A female patient 67 years of age; a dermoscopic image of a skin lesion; the patient says their skin tans without first burning: 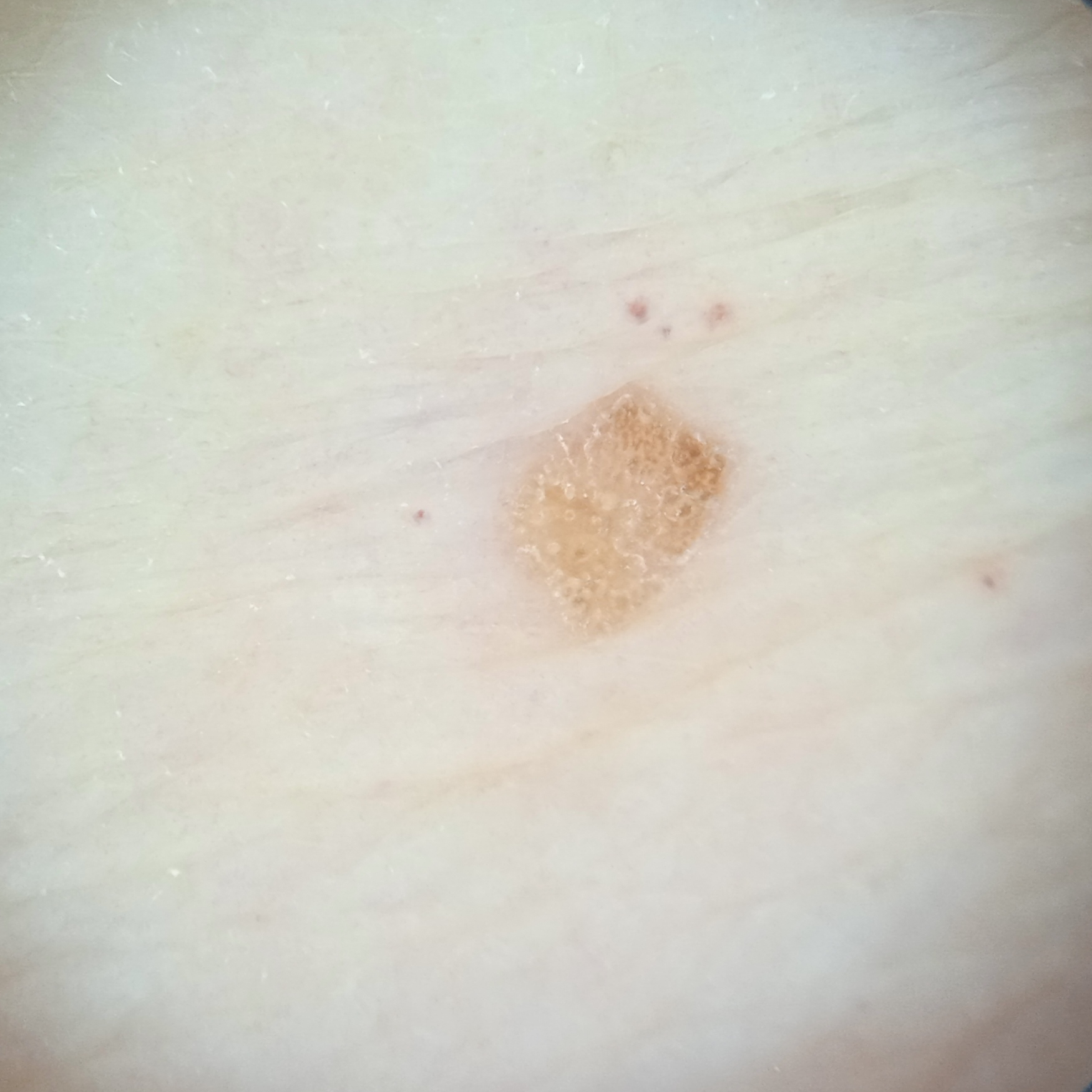Measuring roughly 3.1 mm.
Dermatologist review favored a seborrheic keratosis.